A smartphone photograph of a skin lesion. A male subject 43 years of age: 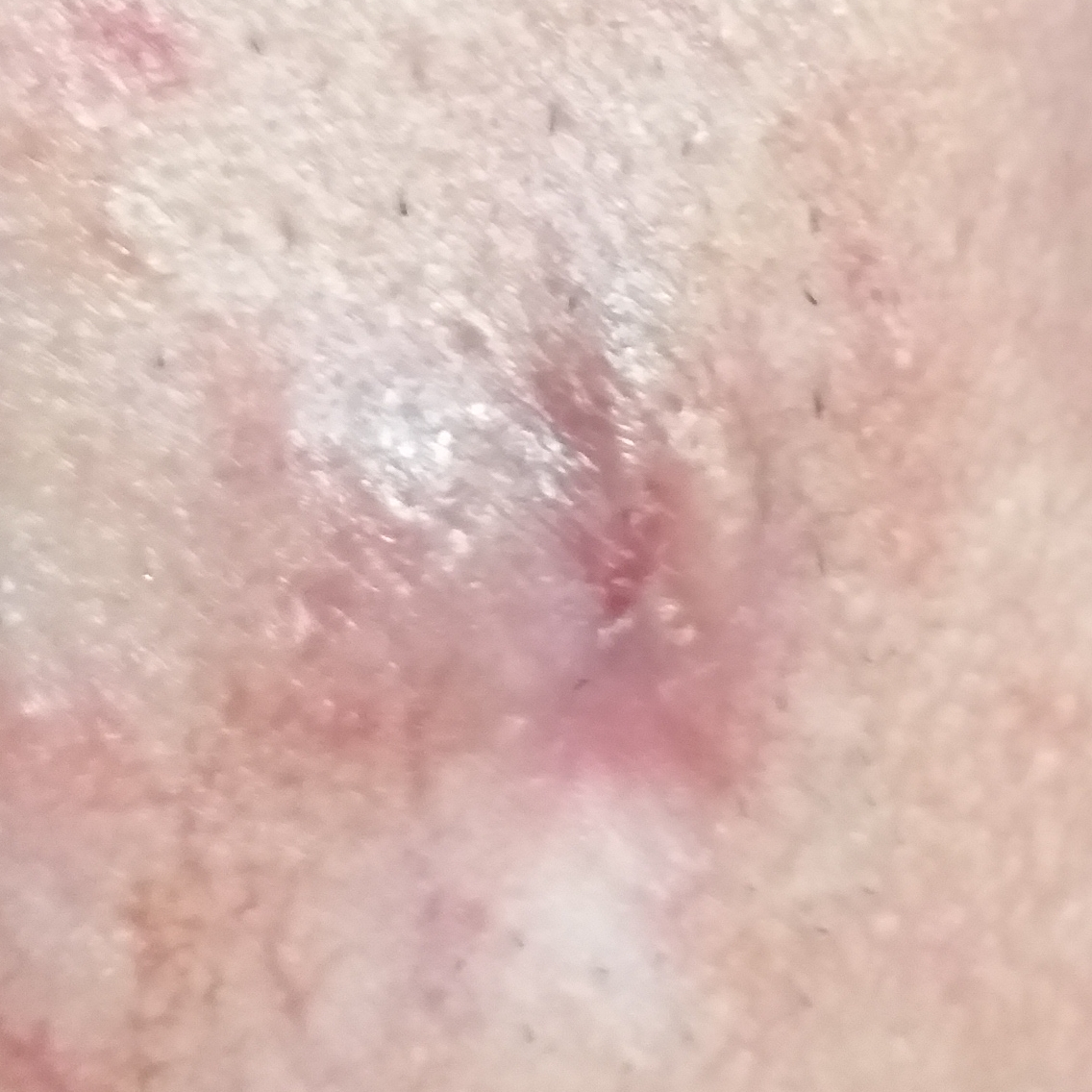  lesion_location: an ear
  symptoms:
    present:
      - bleeding
      - elevation
      - itching
      - growth
  diagnosis:
    name: squamous cell carcinoma
    code: SCC
    malignancy: malignant
    confirmation: histopathology